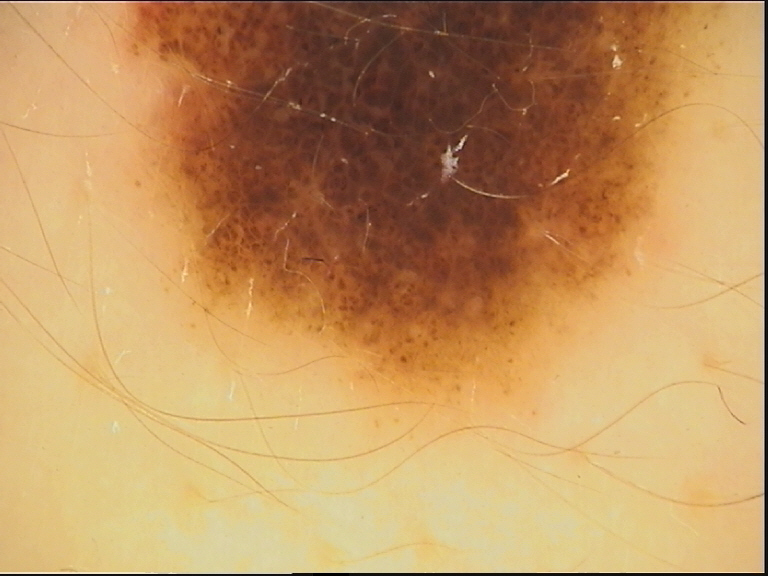| key | value |
|---|---|
| category | banal |
| diagnosis | congenital compound nevus (expert consensus) |